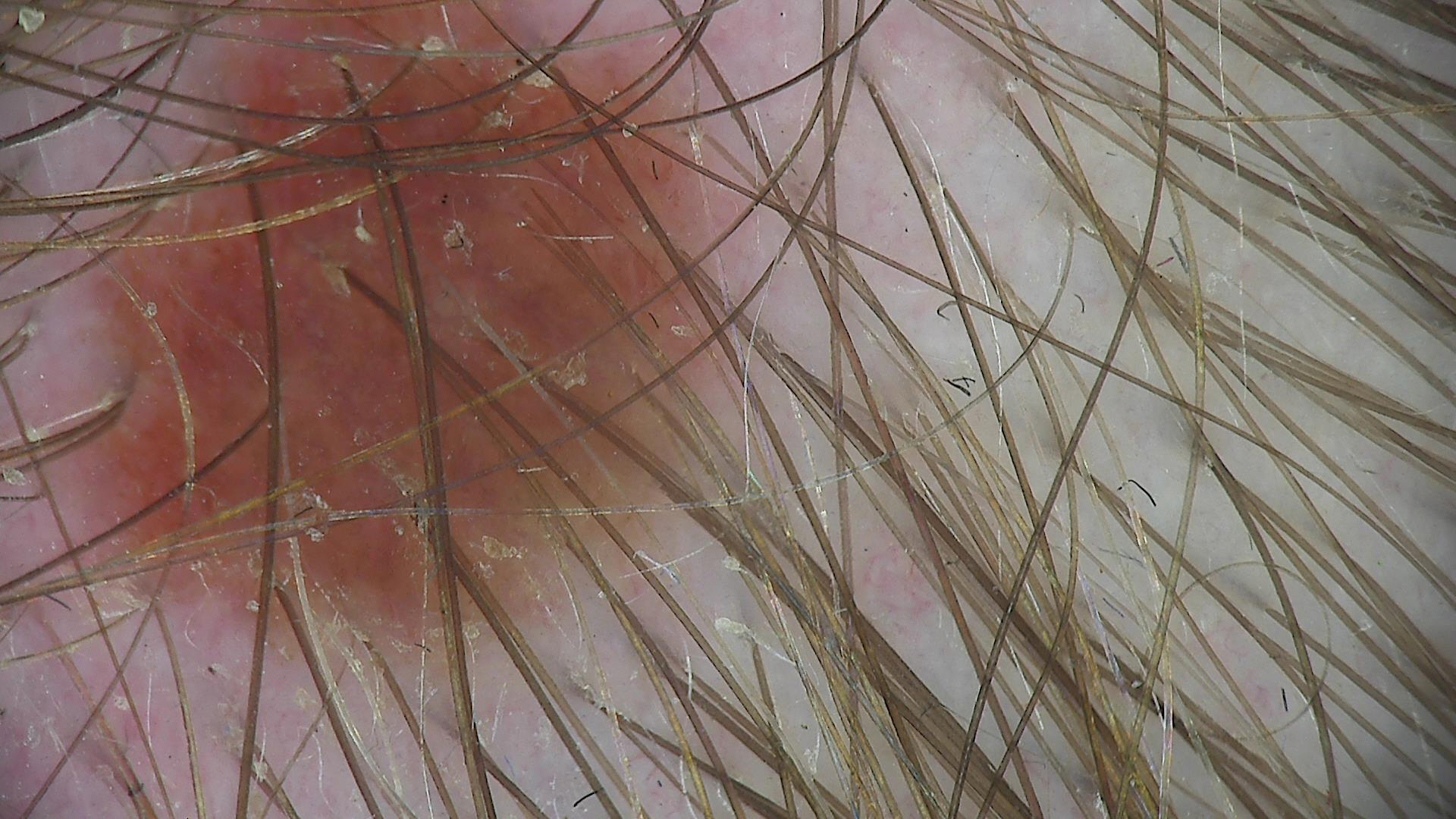A dermoscopy image of a single skin lesion. Classified as a benign lesion — a dysplastic junctional nevus.